A dermoscopic photograph of a skin lesion.
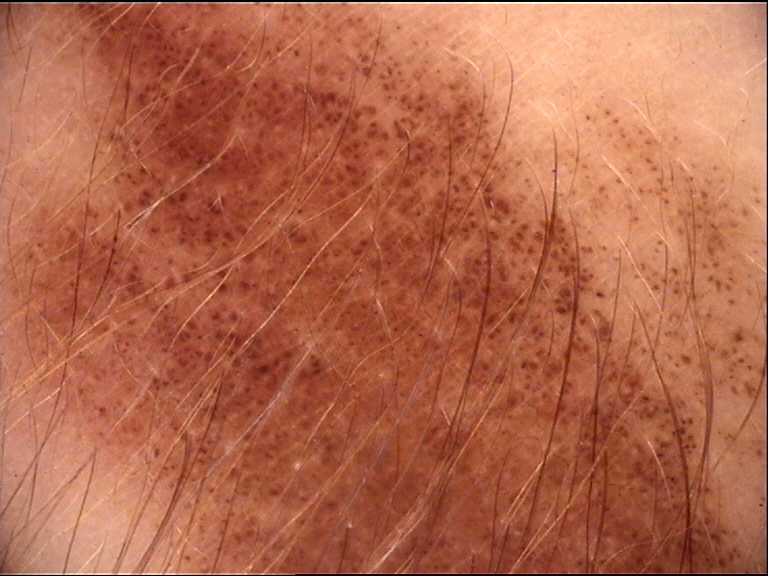class: congenital junctional nevus (expert consensus)